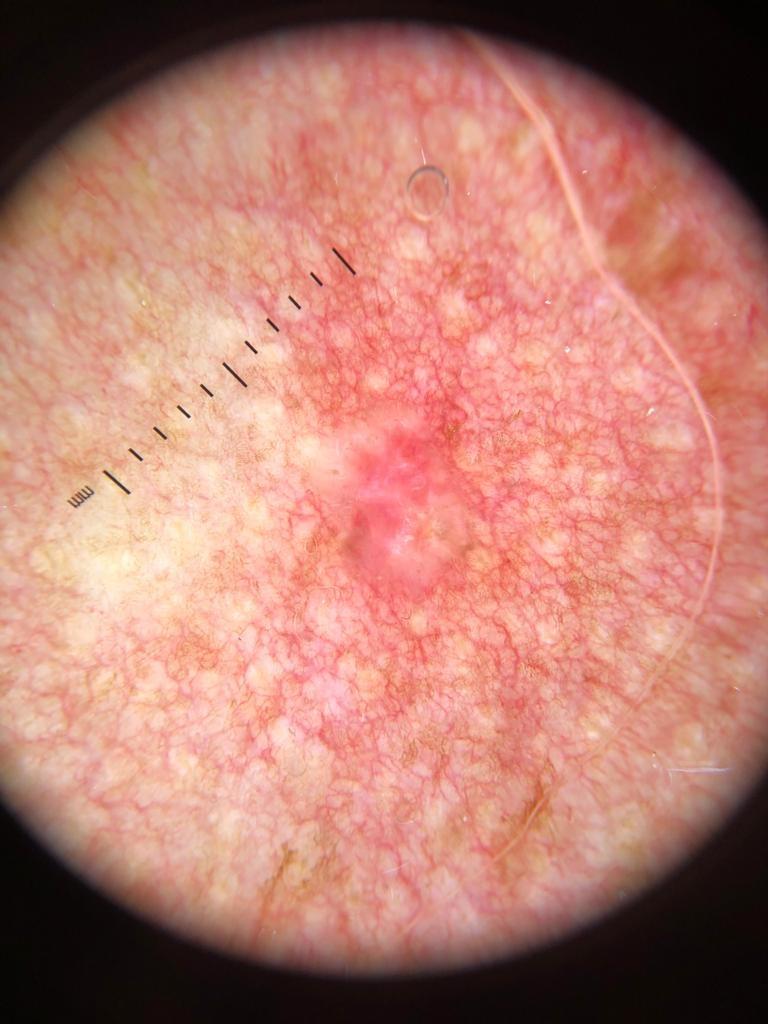Case:
• modality: dermatoscopic image
• patient: female, about 50 years old
• anatomic site: the trunk
• diagnosis: Basal cell carcinoma (biopsy-proven)